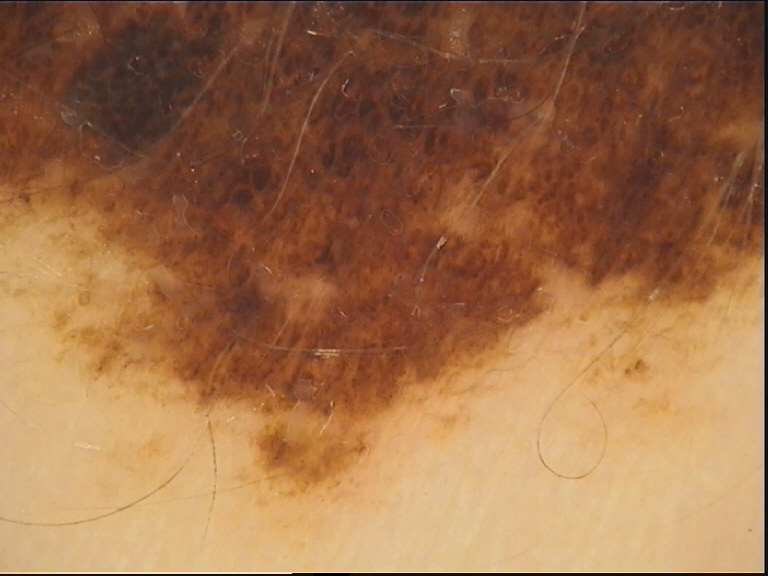The architecture is that of a banal lesion.
Labeled as a congenital compound nevus.